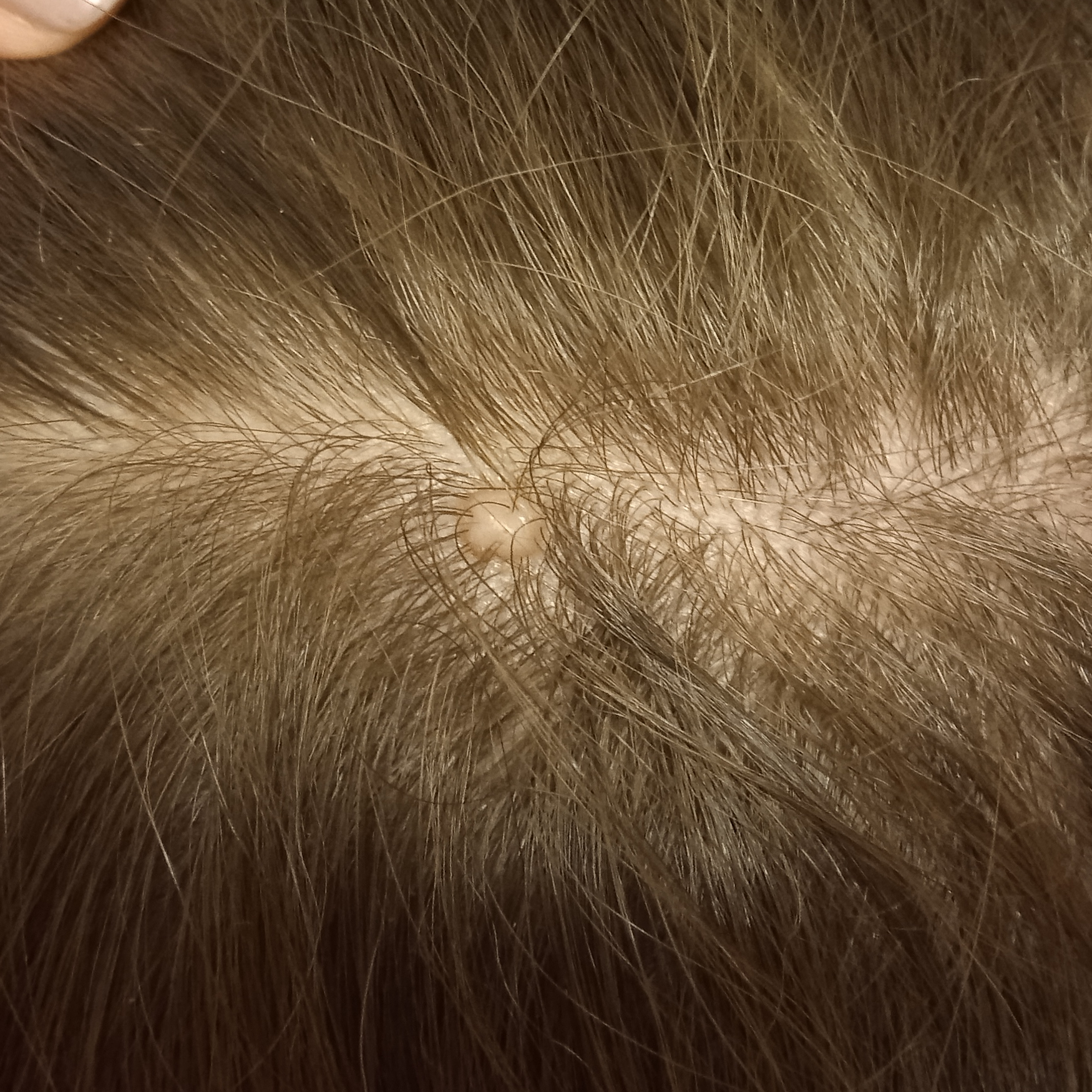Diagnosis: Histopathology confirmed a melanocytic nevus, following excision.